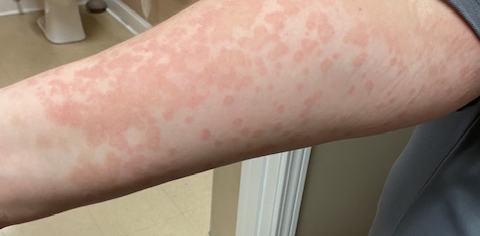On remote review of the image: Drug Rash (considered); Urticaria (considered); Leukocytoclastic Vasculitis (considered).